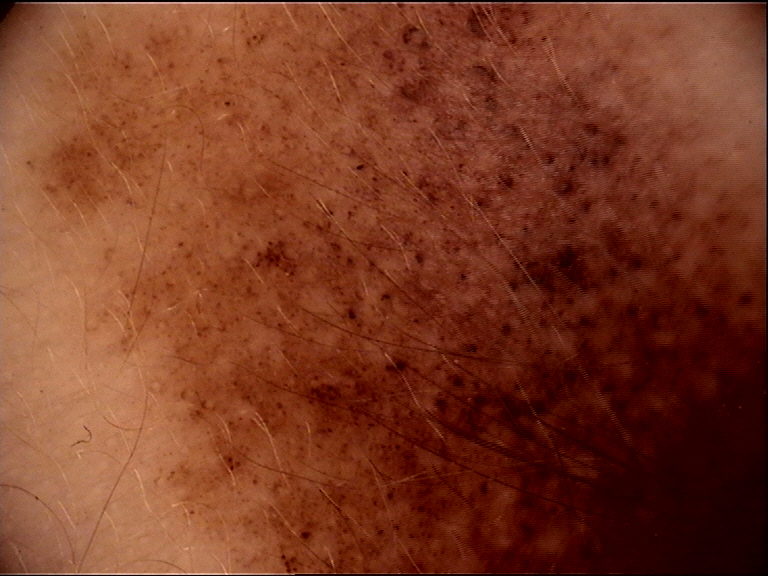image: dermoscopy
class: congenital compound nevus (expert consensus)